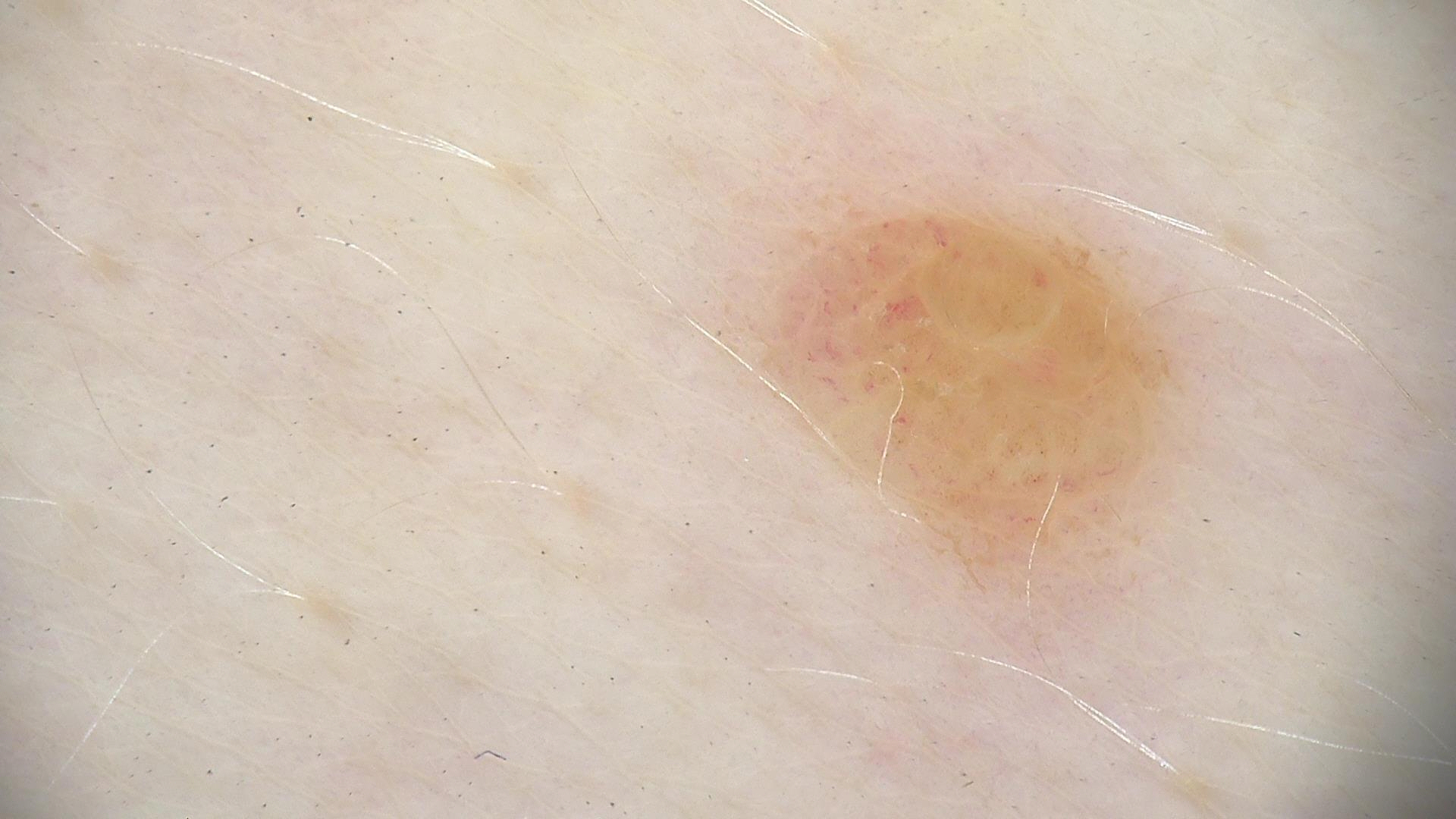| key | value |
|---|---|
| imaging | dermoscopy |
| category | banal |
| assessment | dermal nevus (expert consensus) |